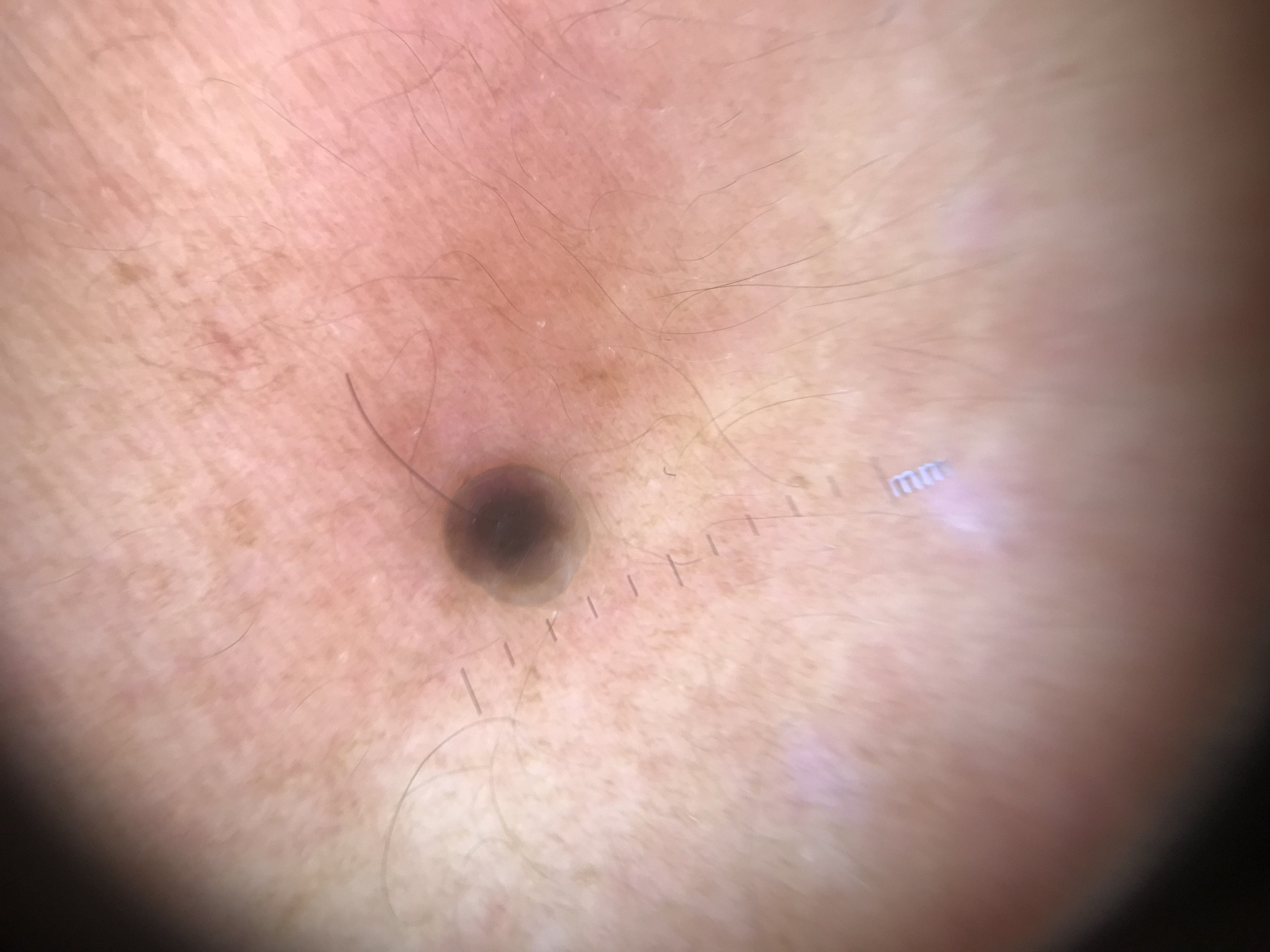imaging=dermoscopy | subtype=banal | assessment=dermal nevus (expert consensus).